A clinical photograph of a skin lesion:
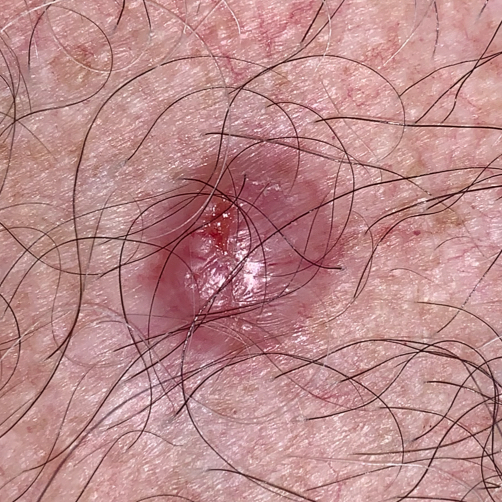Per patient report, the lesion itches, has grown, and is elevated, but does not hurt and has not changed.
Histopathology confirmed a basal cell carcinoma.